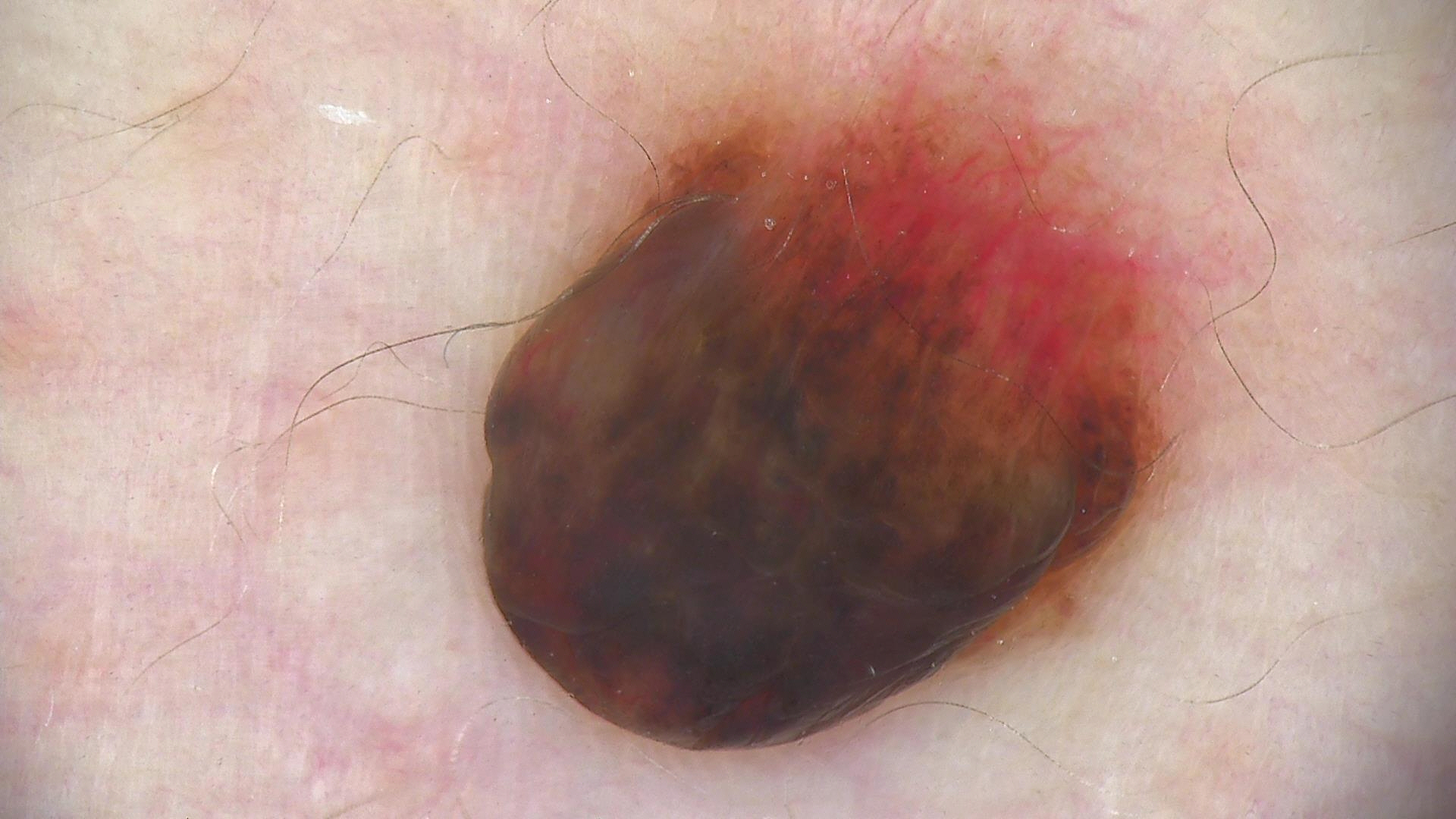<dermoscopy>
  <diagnosis>
    <name>dermal nevus</name>
    <code>db</code>
    <malignancy>benign</malignancy>
    <super_class>melanocytic</super_class>
    <confirmation>expert consensus</confirmation>
  </diagnosis>
</dermoscopy>